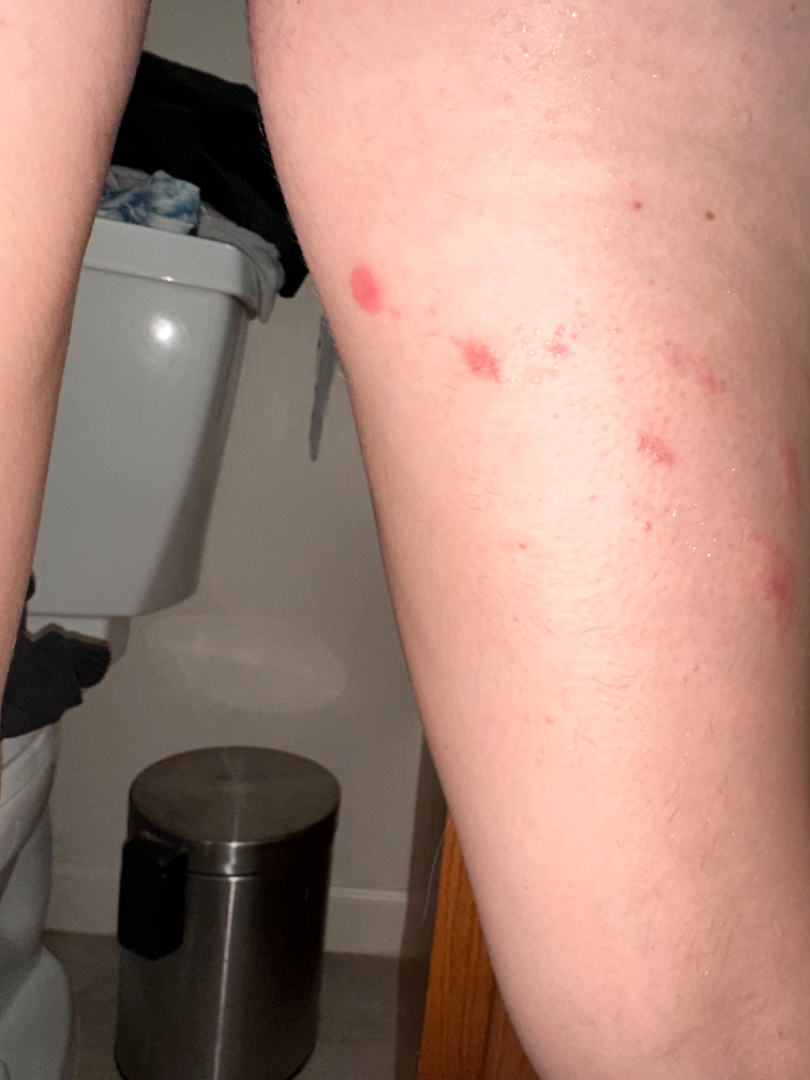<case>
  <duration>less than one week</duration>
  <patient_category>a rash</patient_category>
  <symptoms>itching</symptoms>
  <texture>rough or flaky, raised or bumpy</texture>
  <body_site>leg</body_site>
  <shot_type>close-up</shot_type>
  <differential>
    <Allergic Contact Dermatitis>0.67</Allergic Contact Dermatitis>
    <Eczema>0.33</Eczema>
  </differential>
</case>